The contributor notes the lesion is fluid-filled and raised or bumpy. Fitzpatrick phototype II. The patient considered this a rash. Reported lesion symptoms include itching and pain. The photograph was taken at an angle. Reported duration is less than one week:
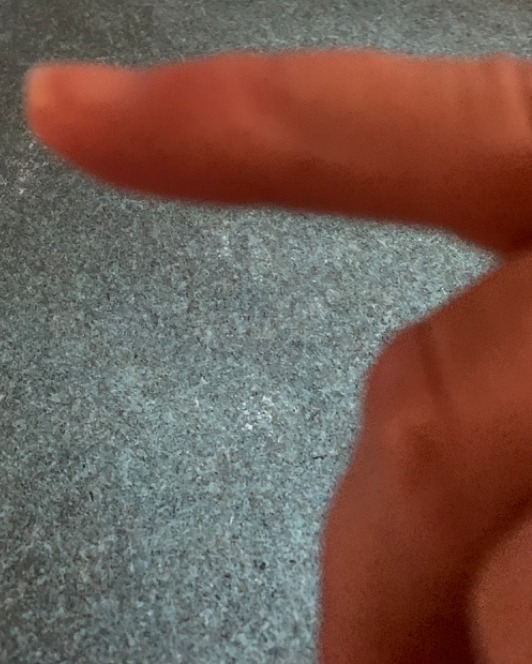assessment = no discernible pathology.